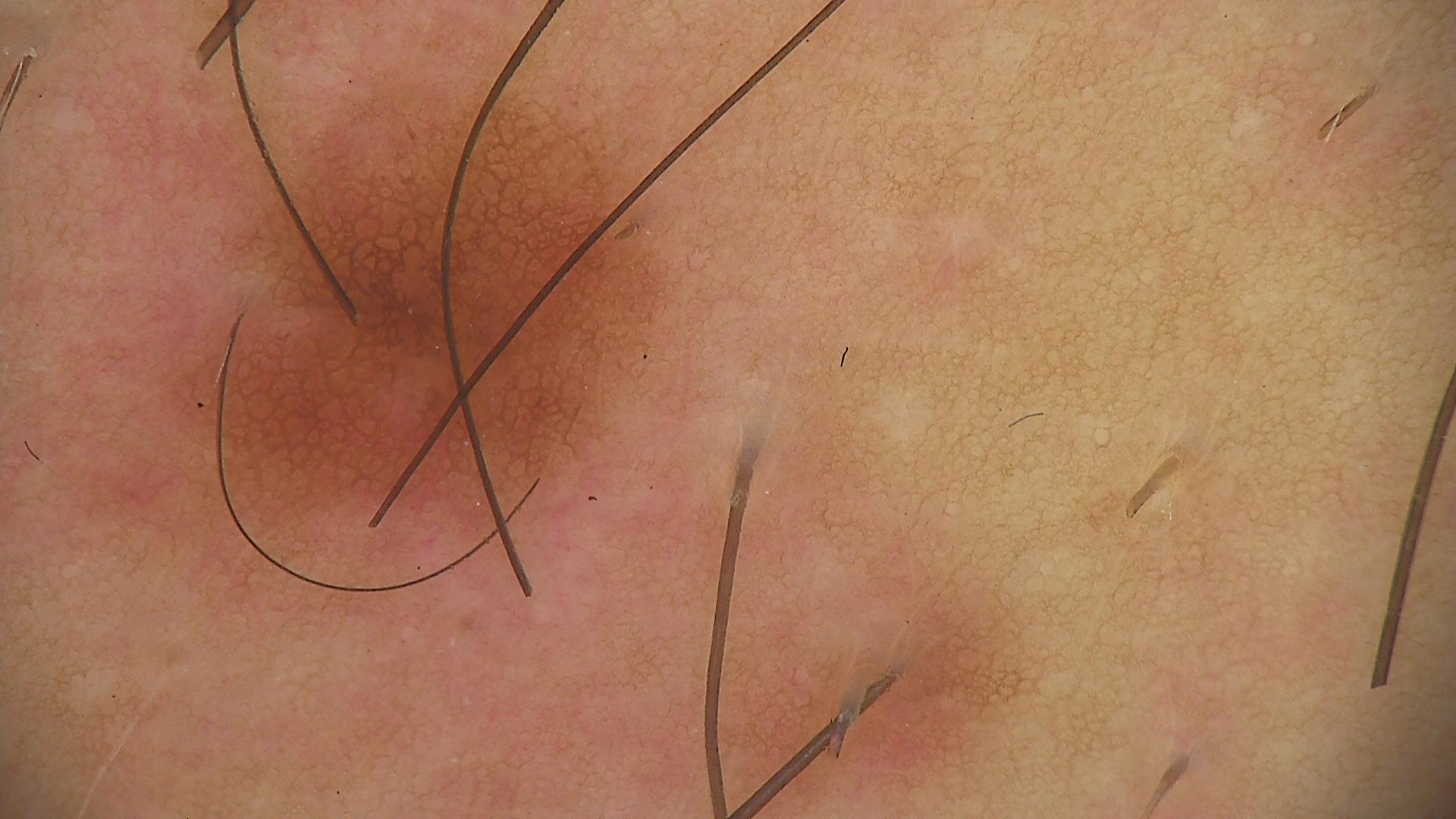A dermatoscopic image of a skin lesion. This is a banal lesion. The diagnosis was a junctional nevus.